A female patient aged 15. A skin lesion imaged with a dermatoscope. Imaged for a research study, with no referral diagnosis recorded: 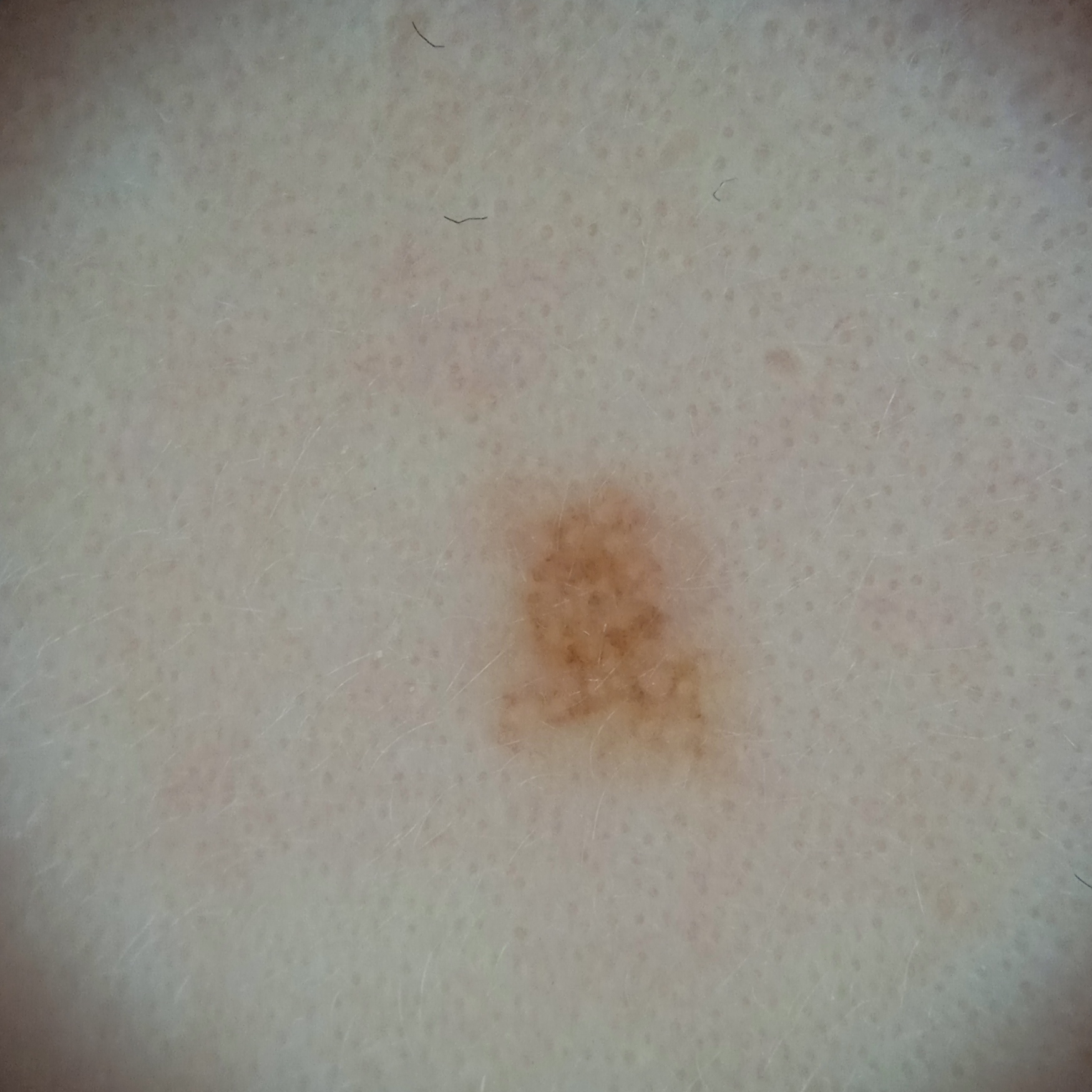Located on the face.
The lesion measures approximately 3.2 mm.
On independent review by four dermatologists, the agreed diagnosis was a melanocytic nevus; the reviewers were moderately confident.